An image taken at a distance, located on the front of the torso — 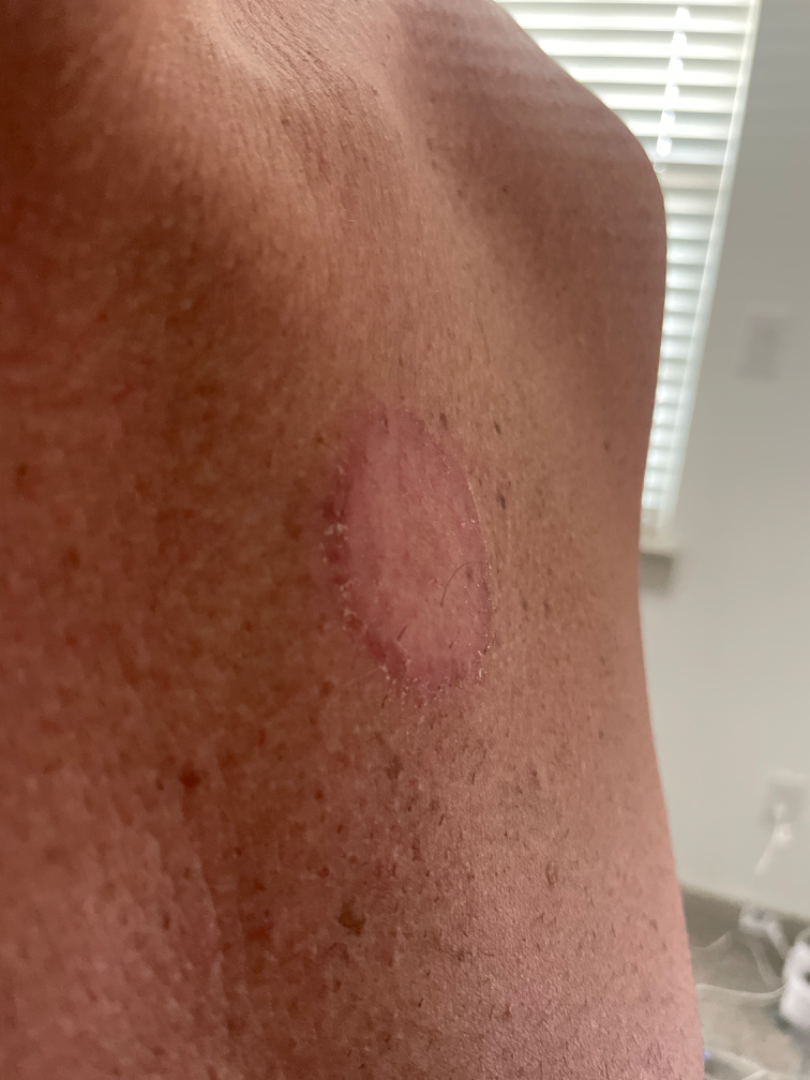<case>
<differential>
  <leading>Tinea</leading>
  <considered>Inflicted skin lesions</considered>
</differential>
</case>